A dermoscopic close-up of a skin lesion: 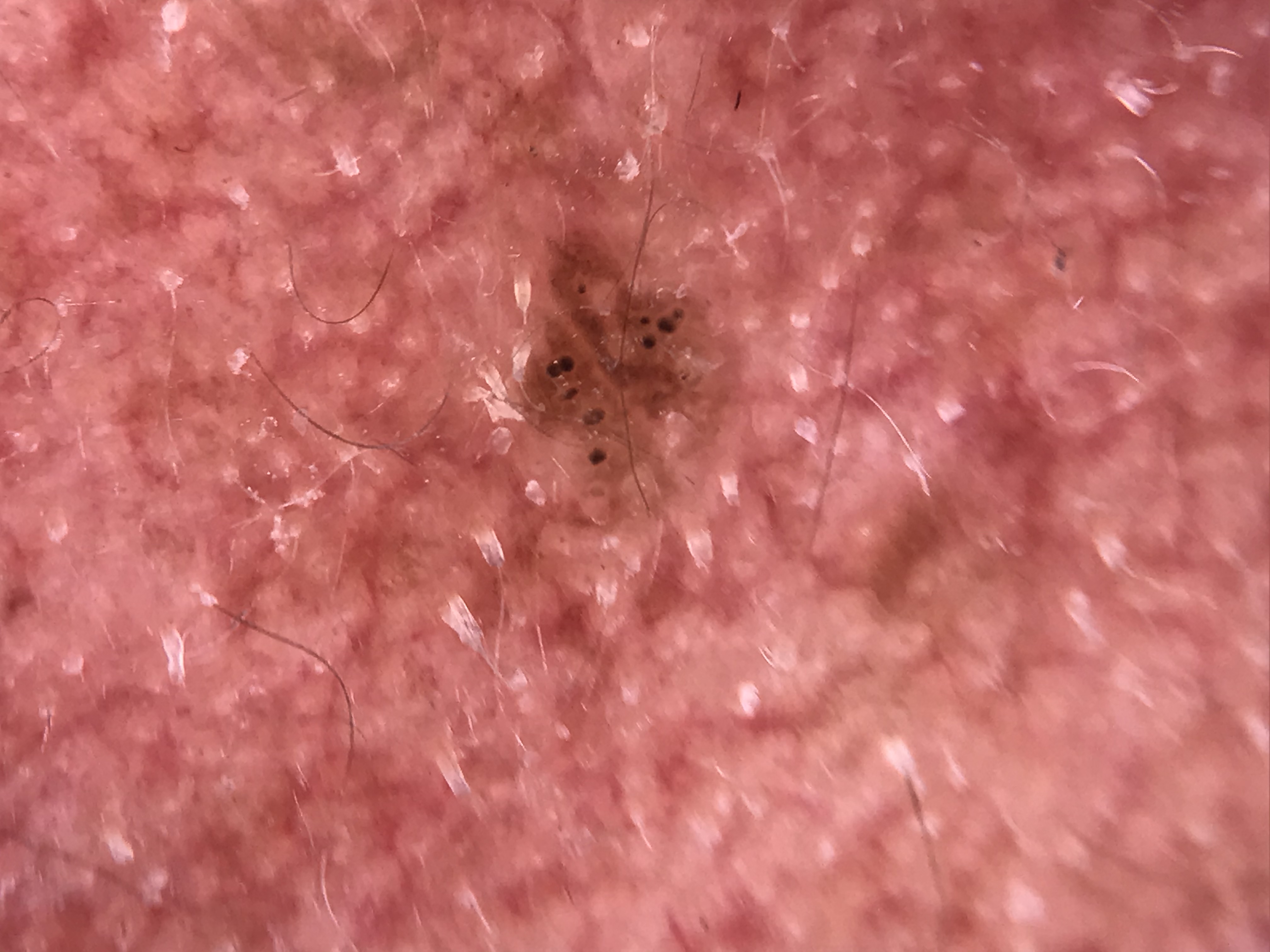Findings:
- classification · keratinocytic
- class · seborrheic keratosis (expert consensus)